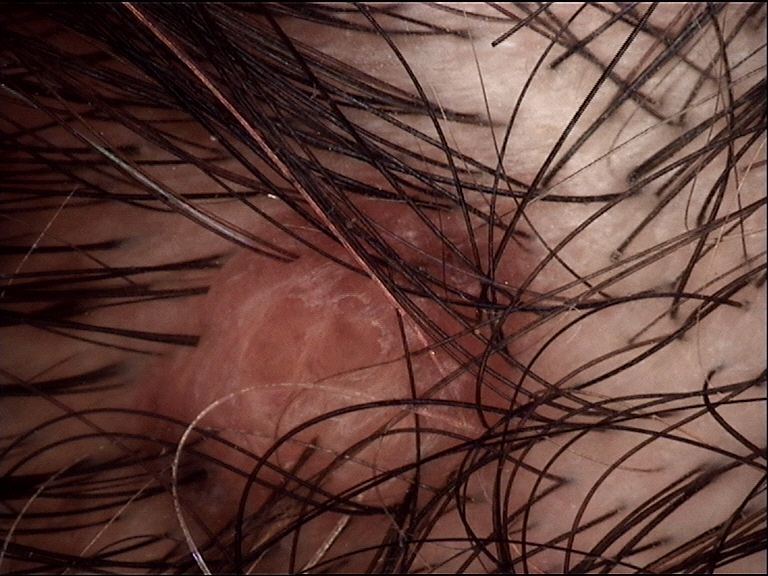A dermoscopy image of a single skin lesion.
The morphology is that of a banal lesion.
The diagnostic label was a dermal nevus.